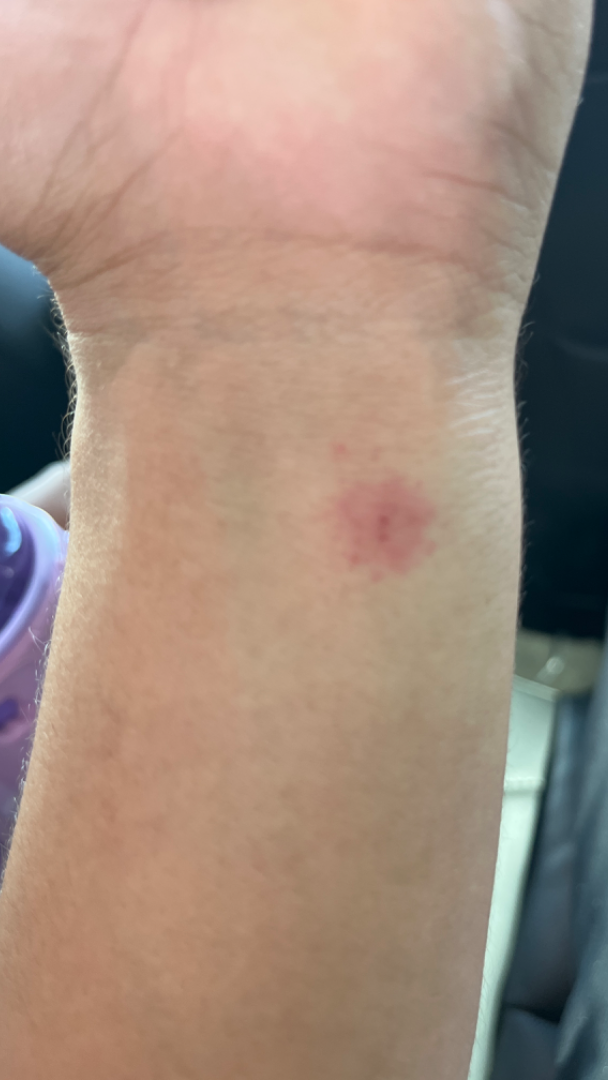Self-categorized by the patient as a rash. No associated systemic symptoms reported. The contributor is male. The lesion is described as raised or bumpy. Skin tone: Fitzpatrick skin type III. A close-up photograph. The arm is involved. The lesion is associated with burning and itching. Most consistent with Insect Bite; also consider Abrasion, scrape, or scab; also raised was Allergic Contact Dermatitis.